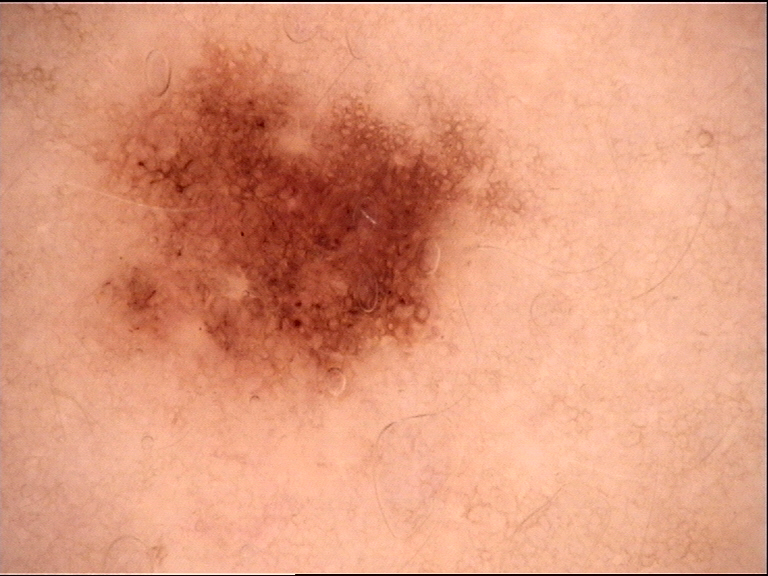diagnostic label = dysplastic junctional nevus (expert consensus).